The photo was captured at a distance.
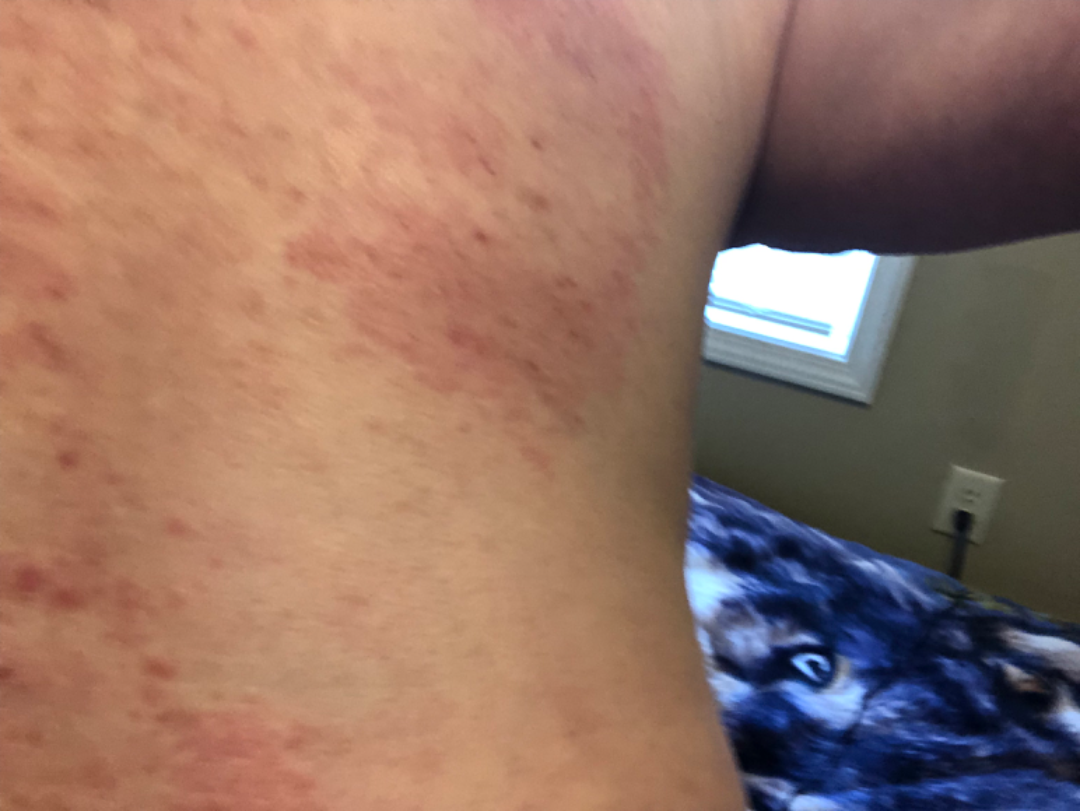| feature | finding |
|---|---|
| assessment | the leading impression is Grover's disease |